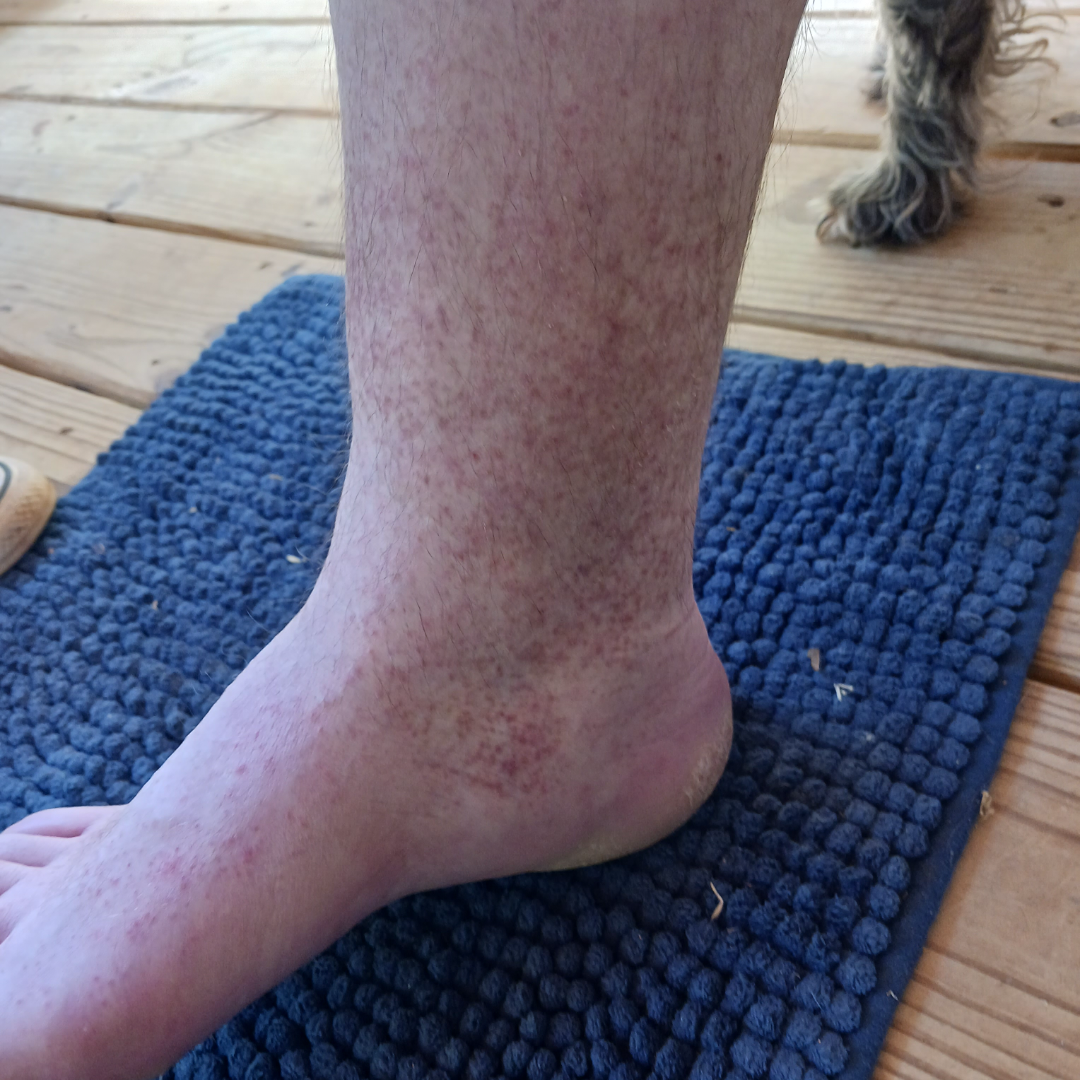differential = Pigmented purpuric eruption, Allergic Contact Dermatitis and Leukocytoclastic Vasculitis were each considered, in no particular order